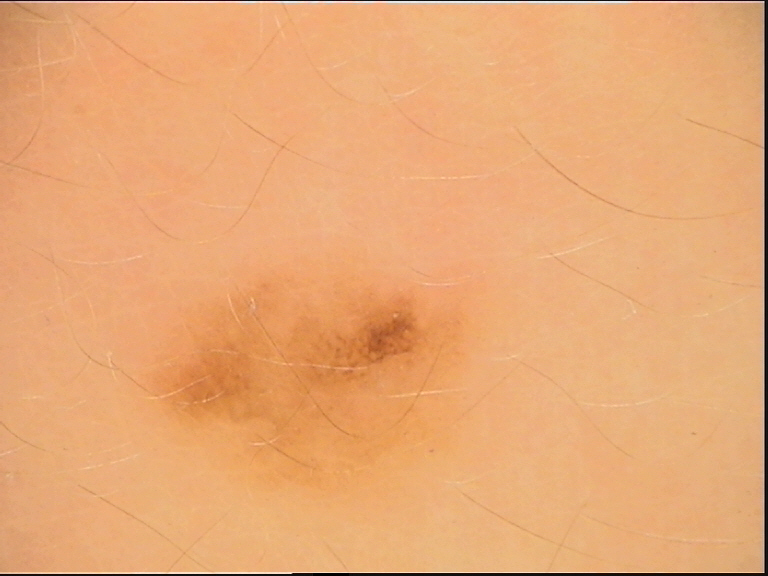modality — dermoscopy; class — dysplastic junctional nevus (expert consensus).